The patient is a male aged 18–29. Close-up view. Located on the arm:
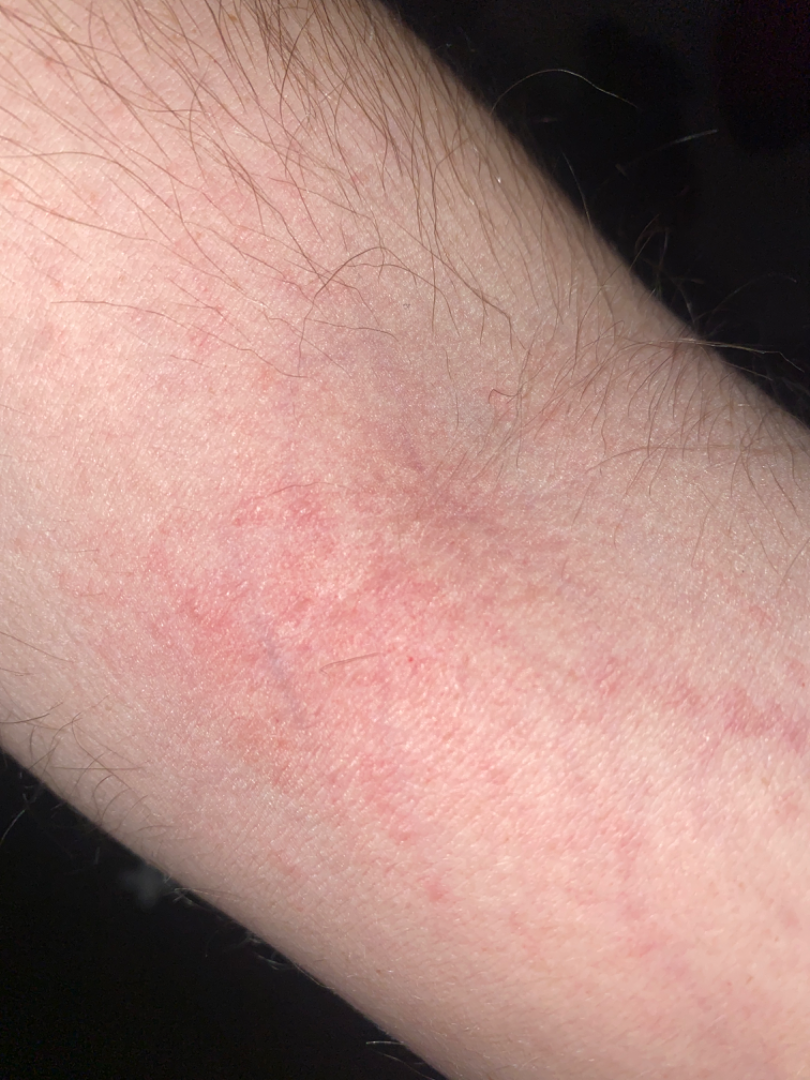<case>
<differential>
  <leading>Eczema</leading>
</differential>
</case>